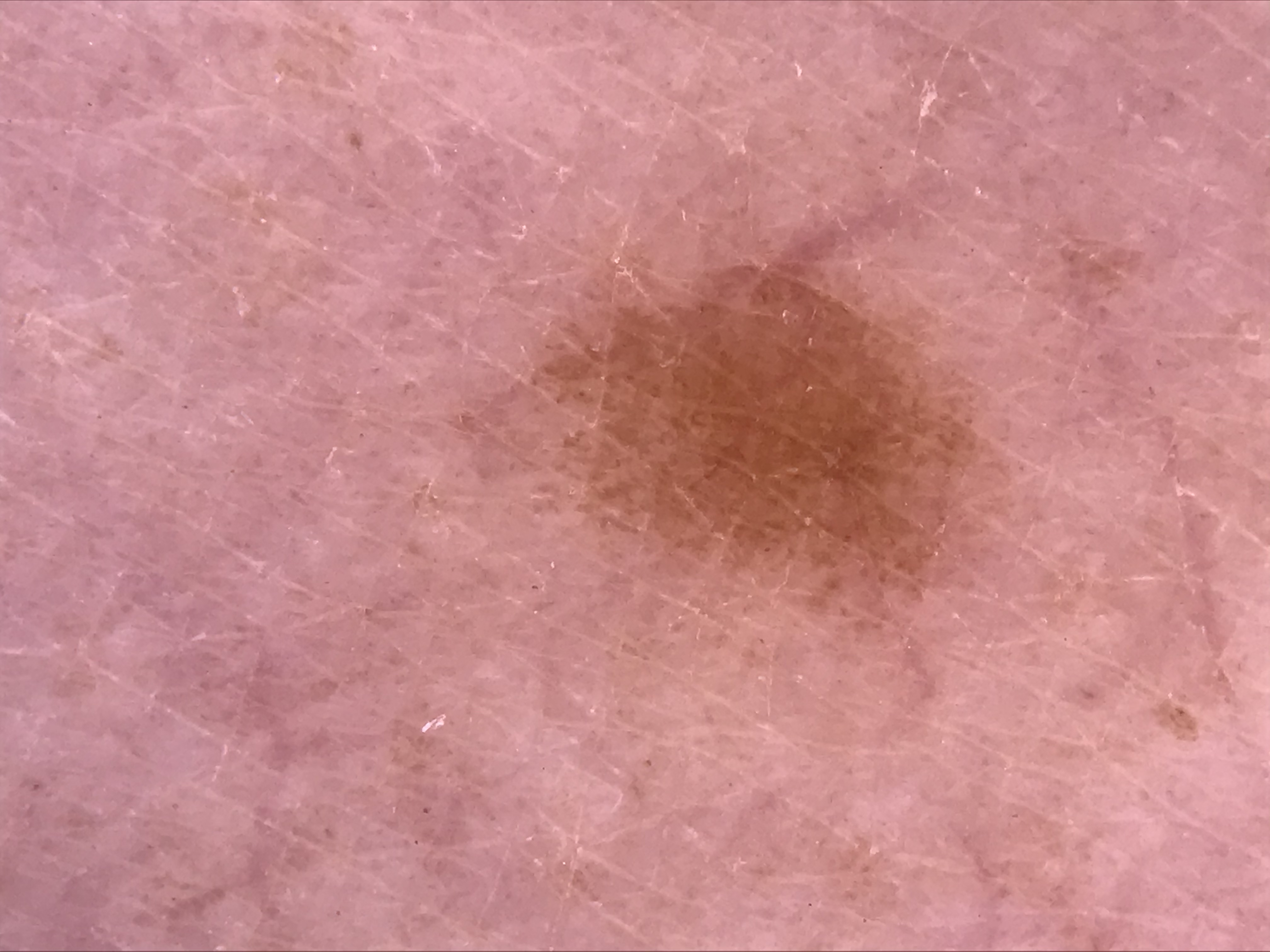Q: What is this lesion?
A: junctional nevus (expert consensus)